The lesion is associated with itching · self-categorized by the patient as a rash · the patient notes the lesion is flat and raised or bumpy · the patient notes the condition has been present for less than one week · the patient reported no systemic symptoms · the subject is a male aged 18–29 · a close-up photograph · the leg is involved — 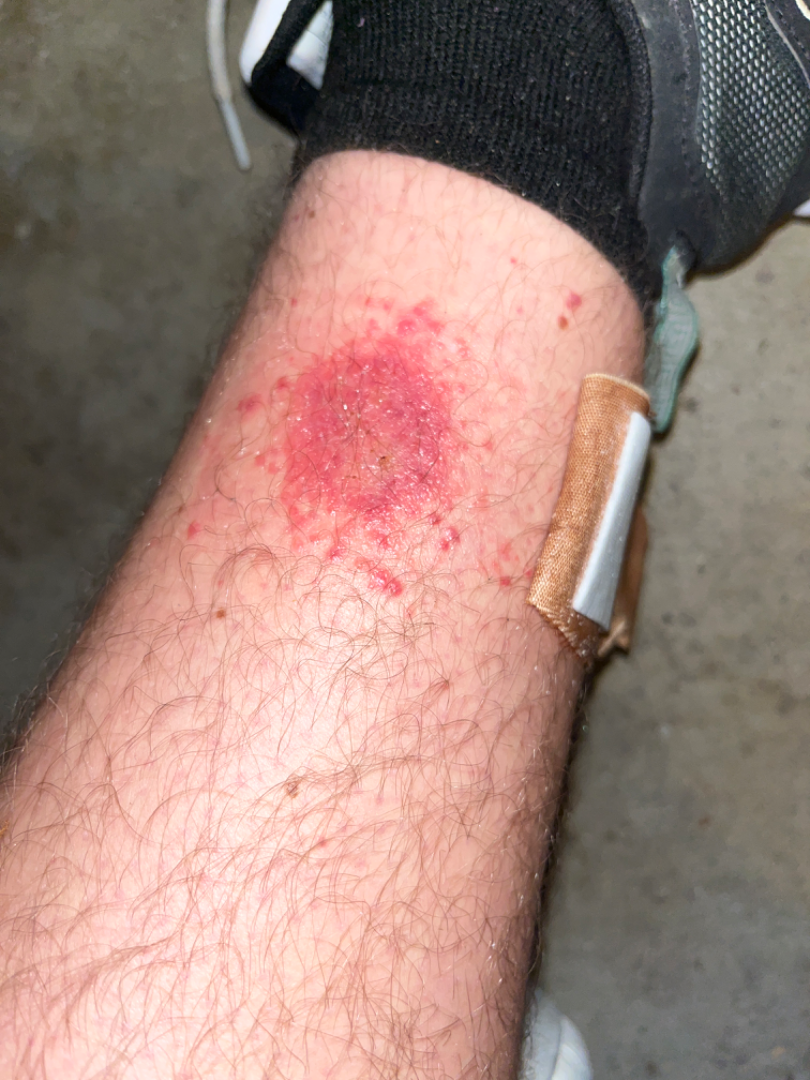assessment = consistent with Allergic Contact Dermatitis.